A skin lesion imaged with a dermatoscope: 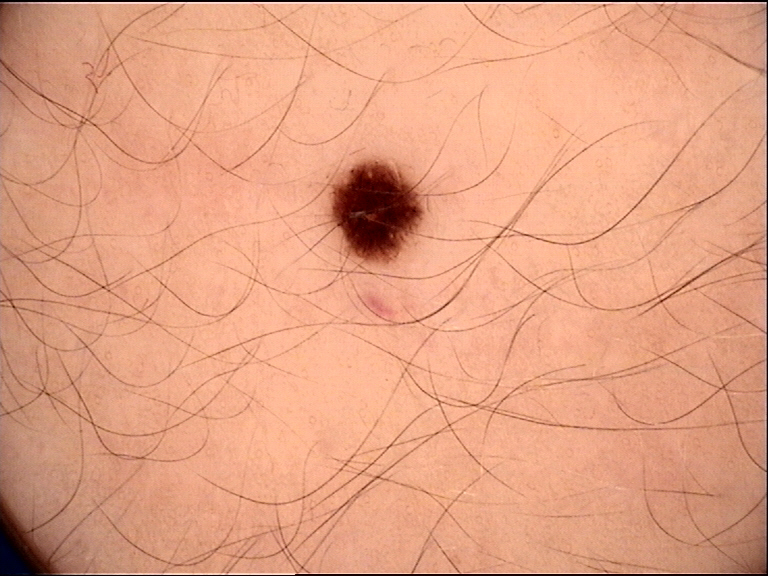Case:
The architecture is that of a banal lesion.
Impression:
Labeled as a junctional nevus.